A dermoscopic image of a skin lesion · a male subject approximately 15 years of age:
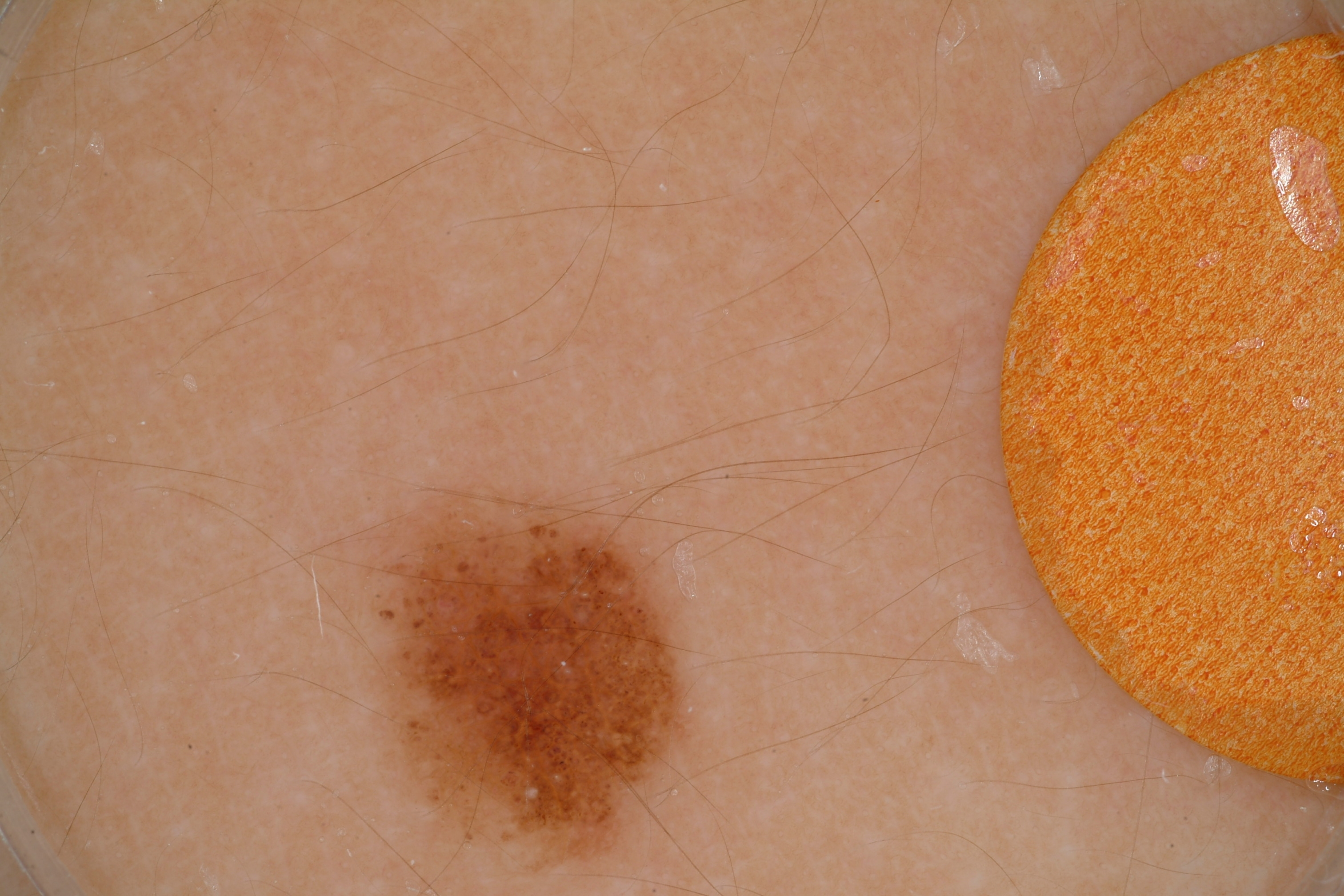Q: Where is the lesion located?
A: x1=359 y1=487 x2=699 y2=877
Q: What does dermoscopy show?
A: globules and milia-like cysts
Q: What is the diagnosis?
A: a melanocytic nevus